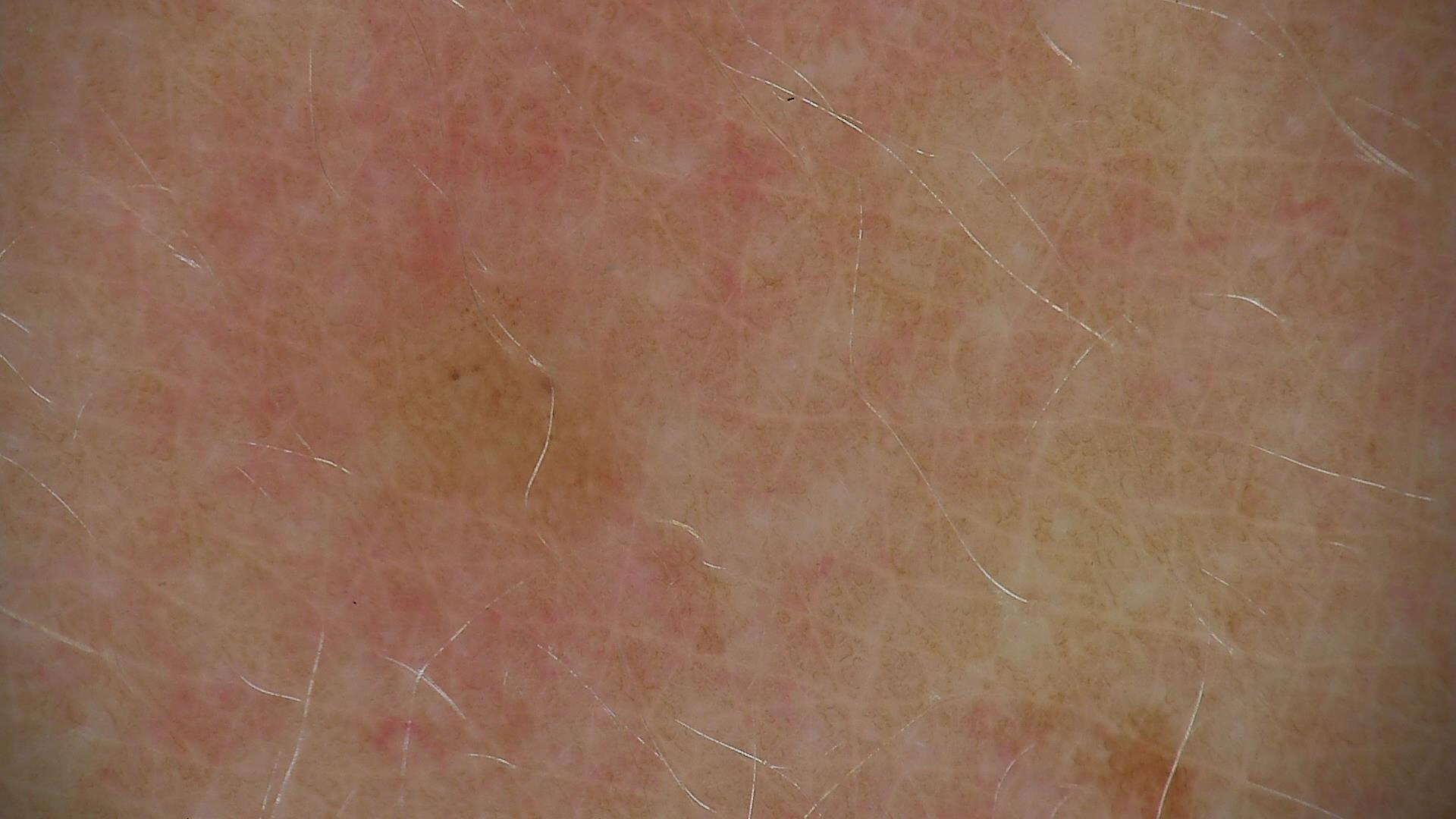A dermatoscopic image of a skin lesion. Consistent with a benign lesion — a dysplastic junctional nevus.